A clinical close-up photograph of a skin lesion; the patient is Fitzpatrick III; history notes prior malignancy (patient or family), tobacco use, prior skin cancer (patient or family), and no pesticide exposure.
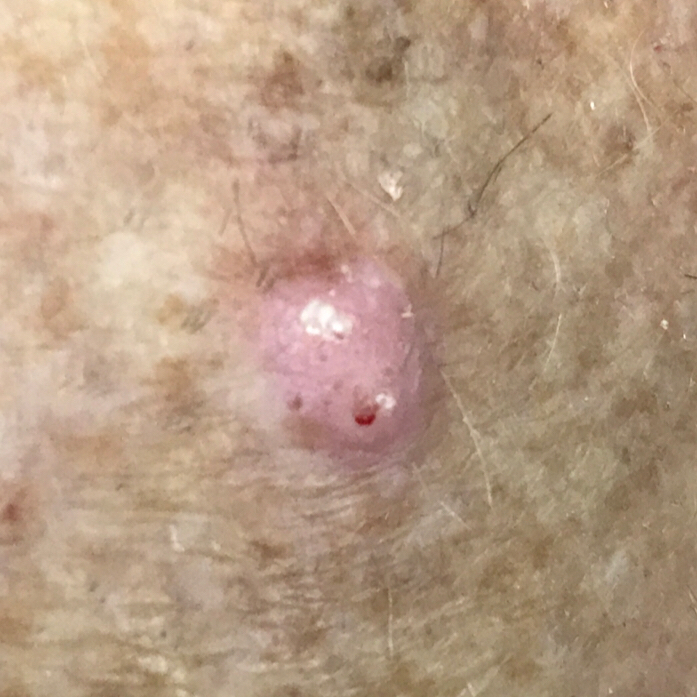The lesion measures 15 × 10 mm.
The patient reports that the lesion is elevated and itches, but does not hurt.
On biopsy, the diagnosis was a malignant skin lesion — a basal cell carcinoma.